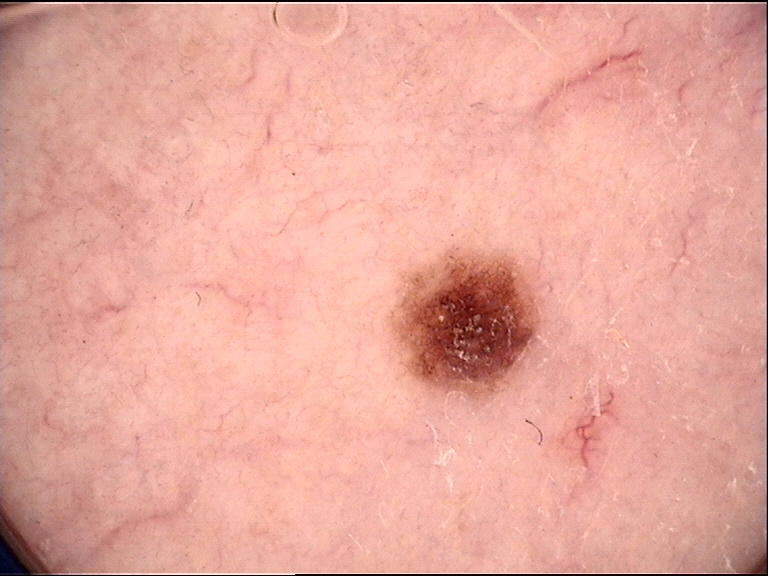Conclusion: The diagnosis was a dysplastic junctional nevus.